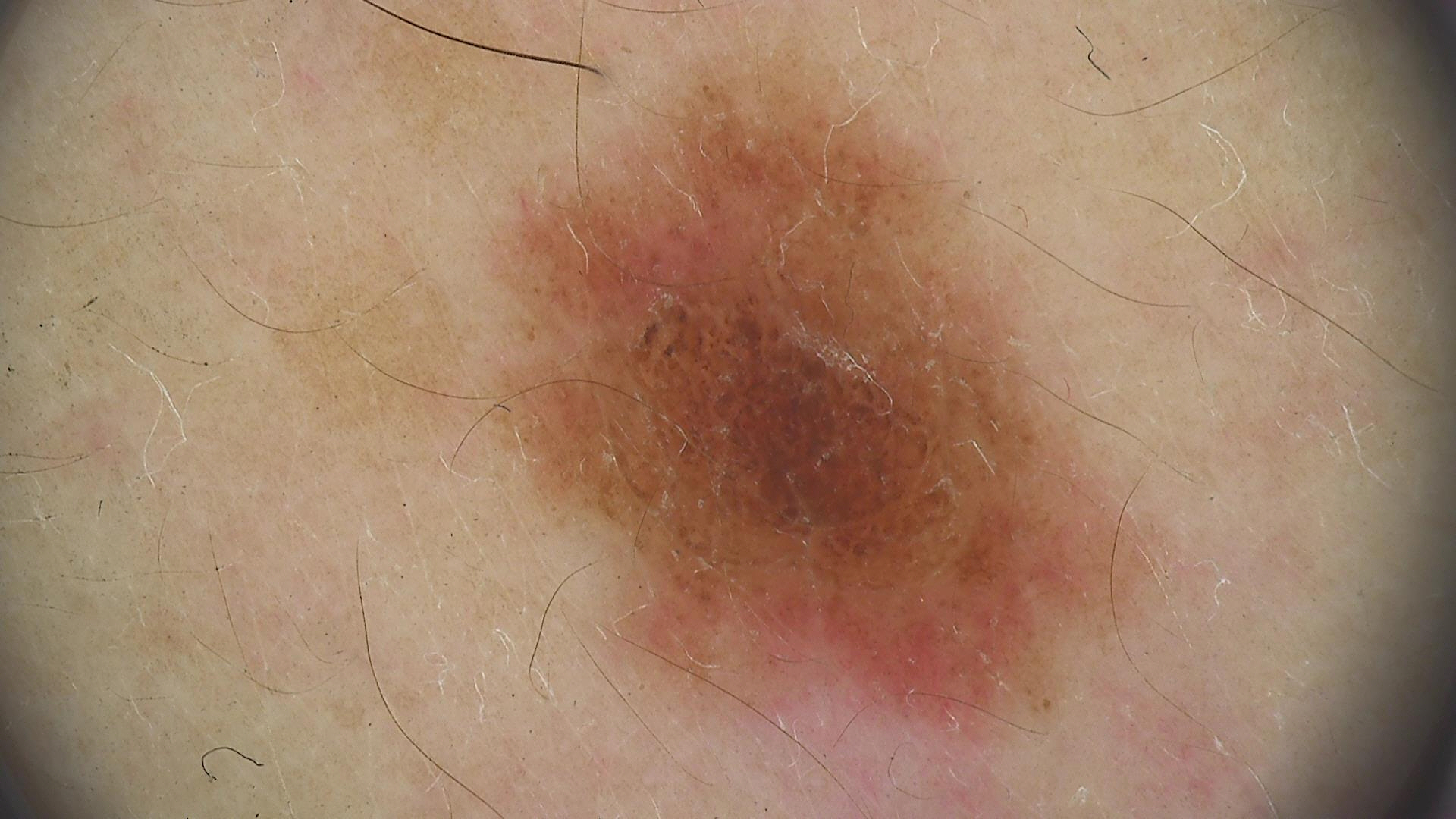Findings:
A dermoscopy image of a single skin lesion. The architecture is that of a banal lesion.
Impression:
Consistent with a compound nevus.